The patient considered this acne, reported lesion symptoms include burning and itching, the affected area is the leg and arm, this image was taken at an angle, the contributor is a female aged 18–29, the patient indicates the lesion is raised or bumpy, the patient indicates the condition has been present for less than one week — 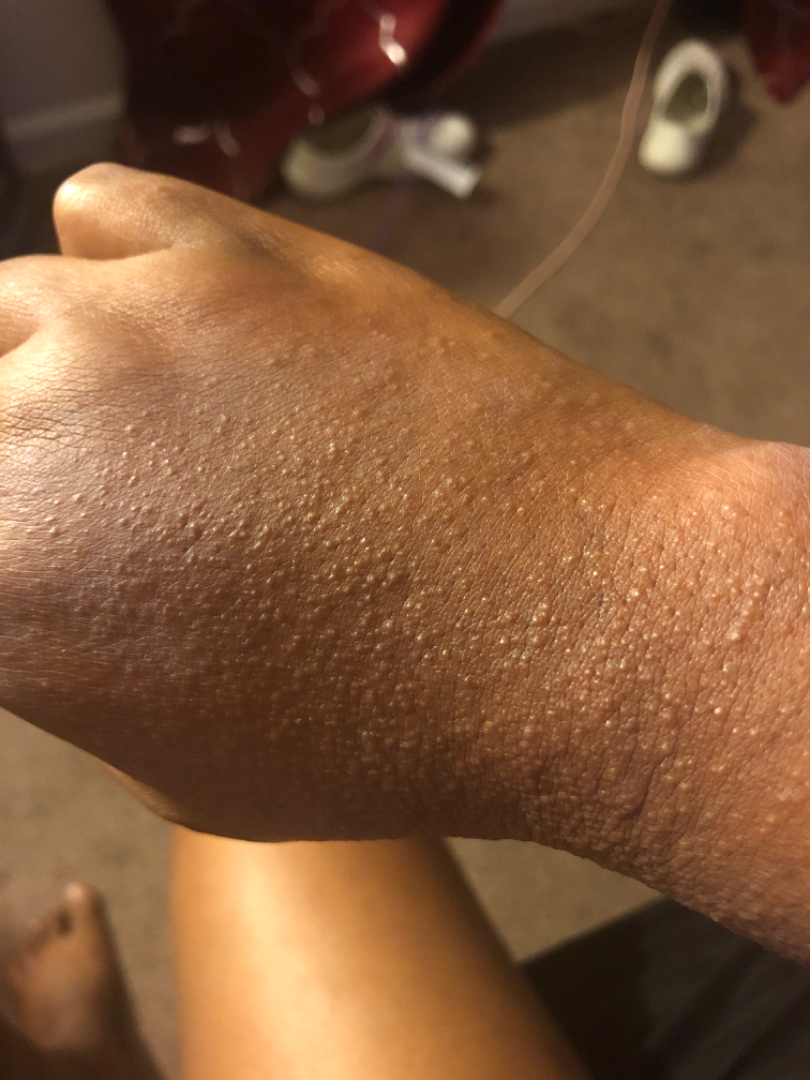Review: On dermatologist assessment of the image: Miliaria and Contact dermatitis, NOS were each considered, in no particular order; less probable is Drug Rash.